A female patient 81 years of age · a moderate number of moles by the patient's own estimate:
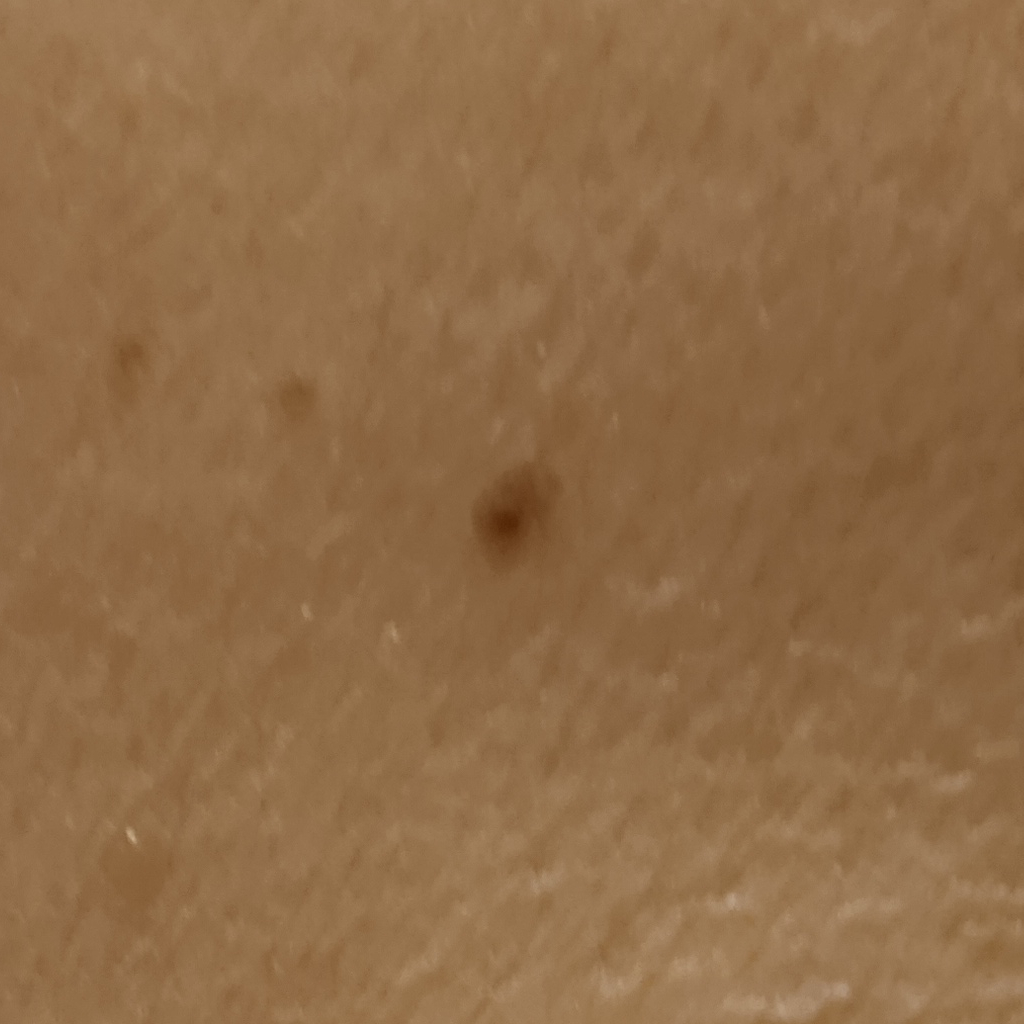The lesion measures approximately 2.7 mm. The dermatologists' assessment was a melanocytic nevus.